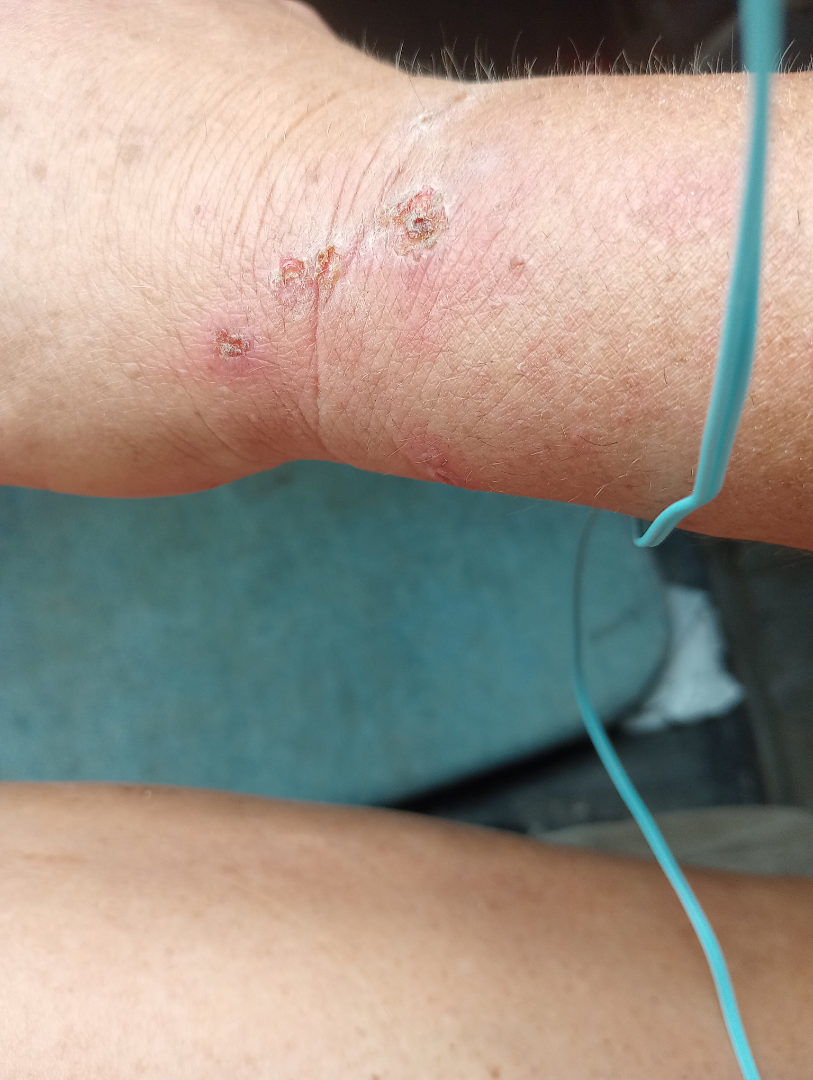The condition could not be reliably identified from the image. The patient described the issue as a rash. The back of the hand is involved. The photograph is a close-up of the affected area. The lesion is associated with itching and bothersome appearance. No associated systemic symptoms reported. The lesion is described as raised or bumpy and rough or flaky. The contributor is a female aged 40–49.